The patient says their skin tans without first burning · referred with a clinical suspicion of basal cell carcinoma · few moles overall by the patient's own estimate · a clinical photograph showing a skin lesion · by self-report, a personal history of cancer, a personal history of skin cancer, and no family history of skin cancer · a female subject 60 years of age:
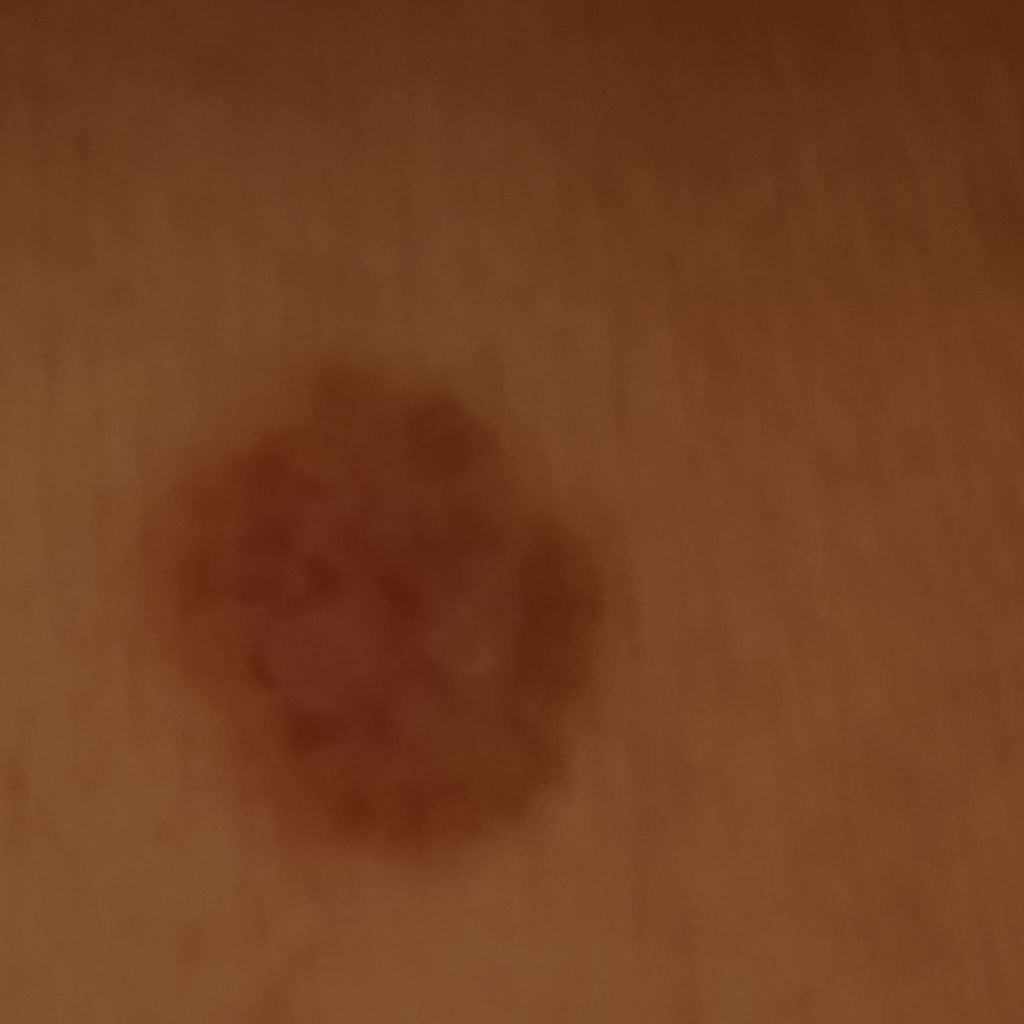location=the torso; diameter=13.2 mm; diagnostic label=basal cell carcinoma (dermatologist consensus).